A dermoscopy image of a single skin lesion: 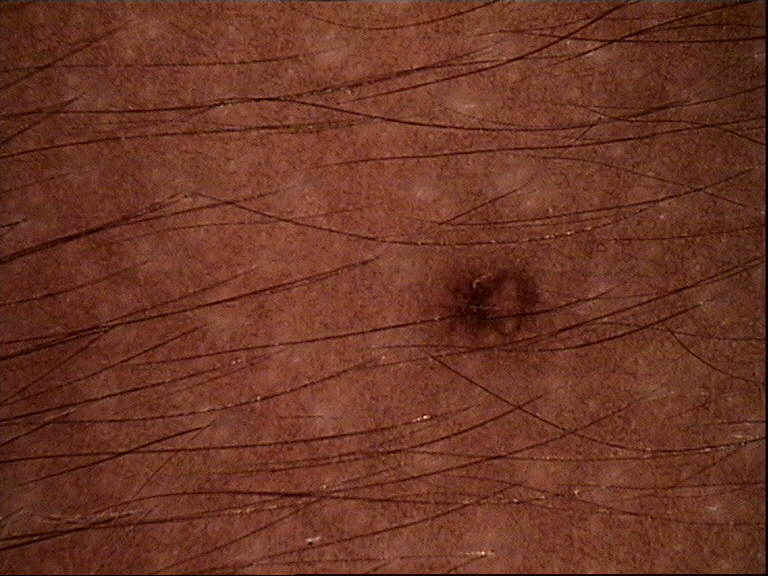This is a banal lesion. Labeled as a junctional nevus.